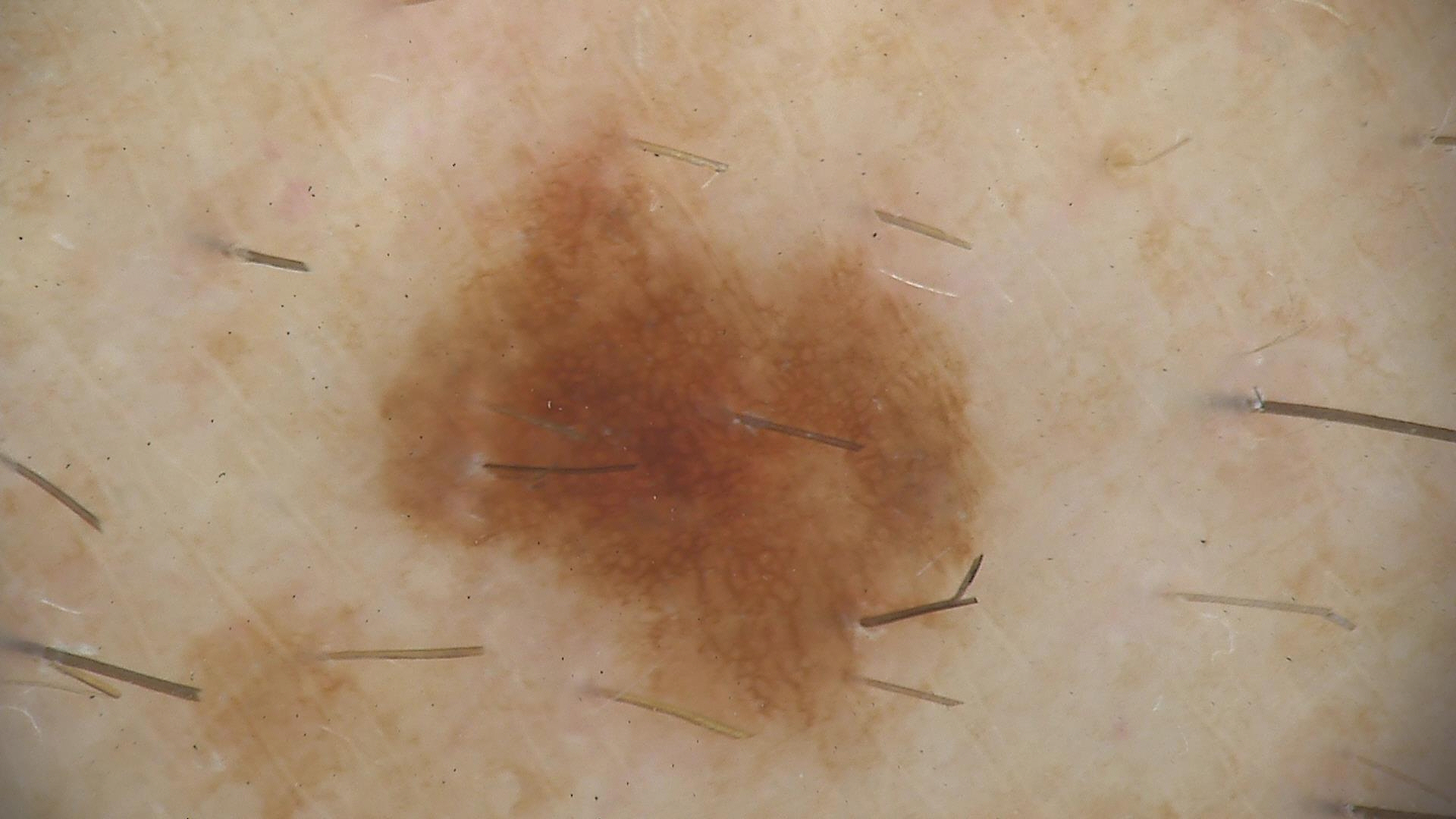The diagnostic label was a dysplastic junctional nevus.